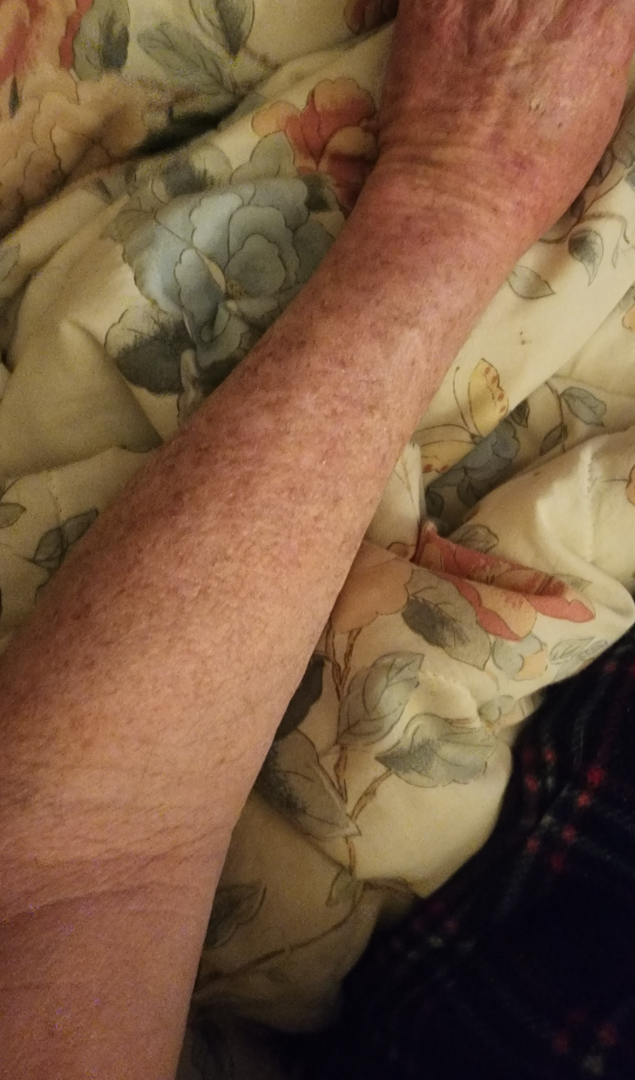No differential diagnosis could be assigned on photographic review.
Male subject, age 60–69.
The photograph was taken at a distance.